Located on the leg and top or side of the foot, an image taken at an angle: 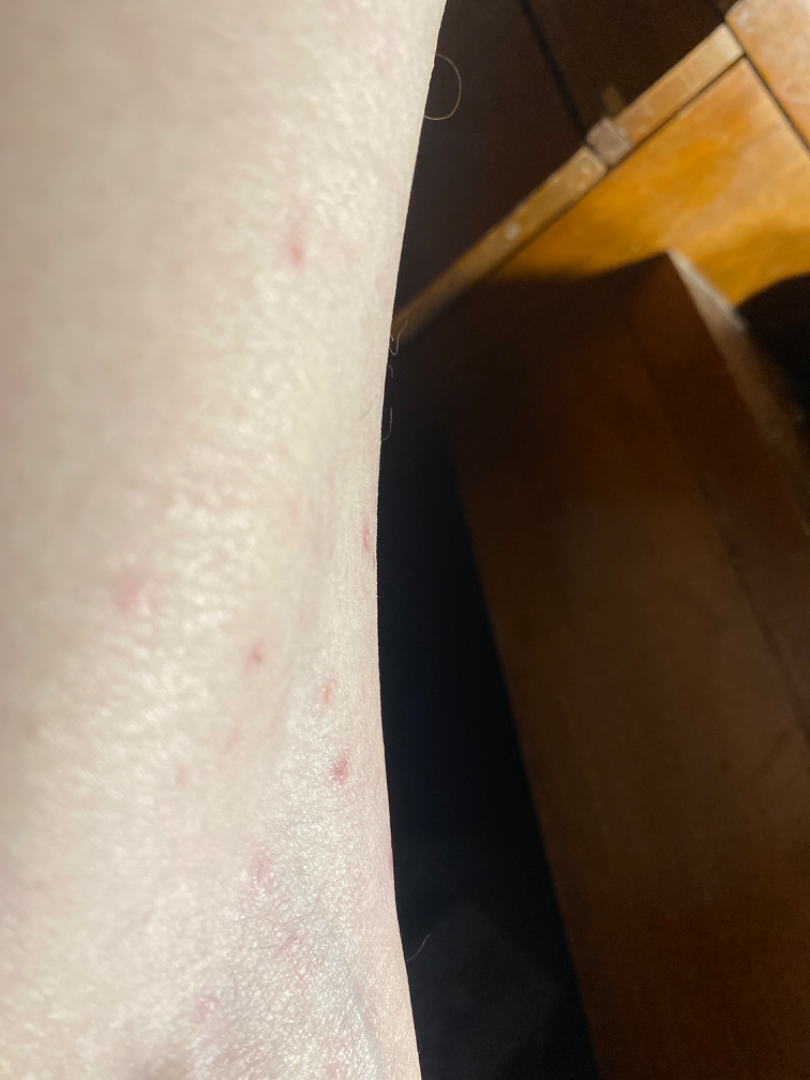The condition has been present for one to four weeks.
Texture is reported as rough or flaky and raised or bumpy.
The patient described the issue as a rash.
Reported lesion symptoms include itching.
One reviewing dermatologist: most consistent with Eczema; also raised was Hypersensitivity.